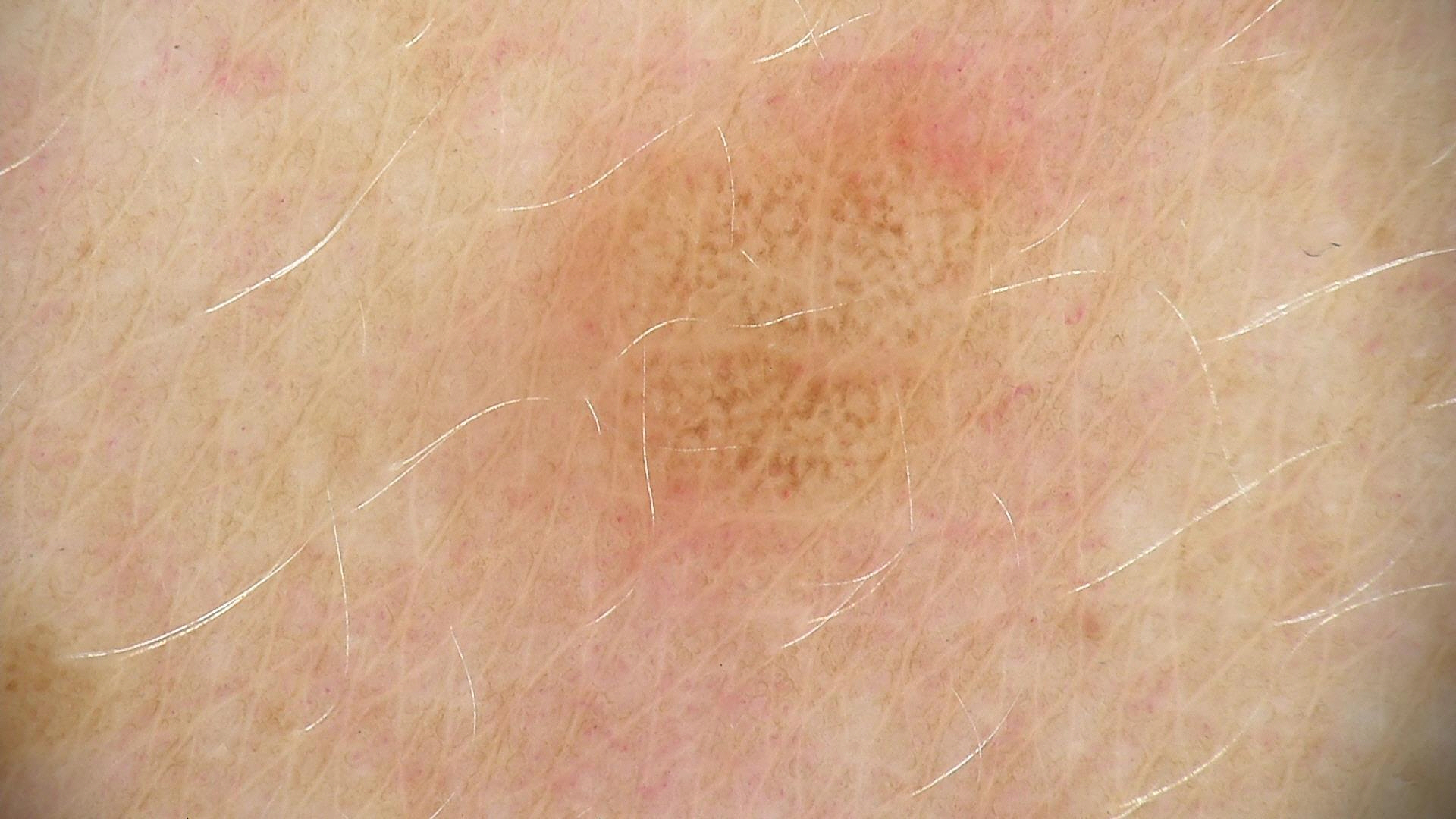  diagnosis:
    name: dysplastic junctional nevus
    code: jd
    malignancy: benign
    super_class: melanocytic
    confirmation: expert consensus